The lesion is described as flat · no constitutional symptoms were reported · the patient notes bothersome appearance · the affected area is the top or side of the foot · female patient, age 40–49 · this is a close-up image · self-categorized by the patient as a rash · present for three to twelve months — 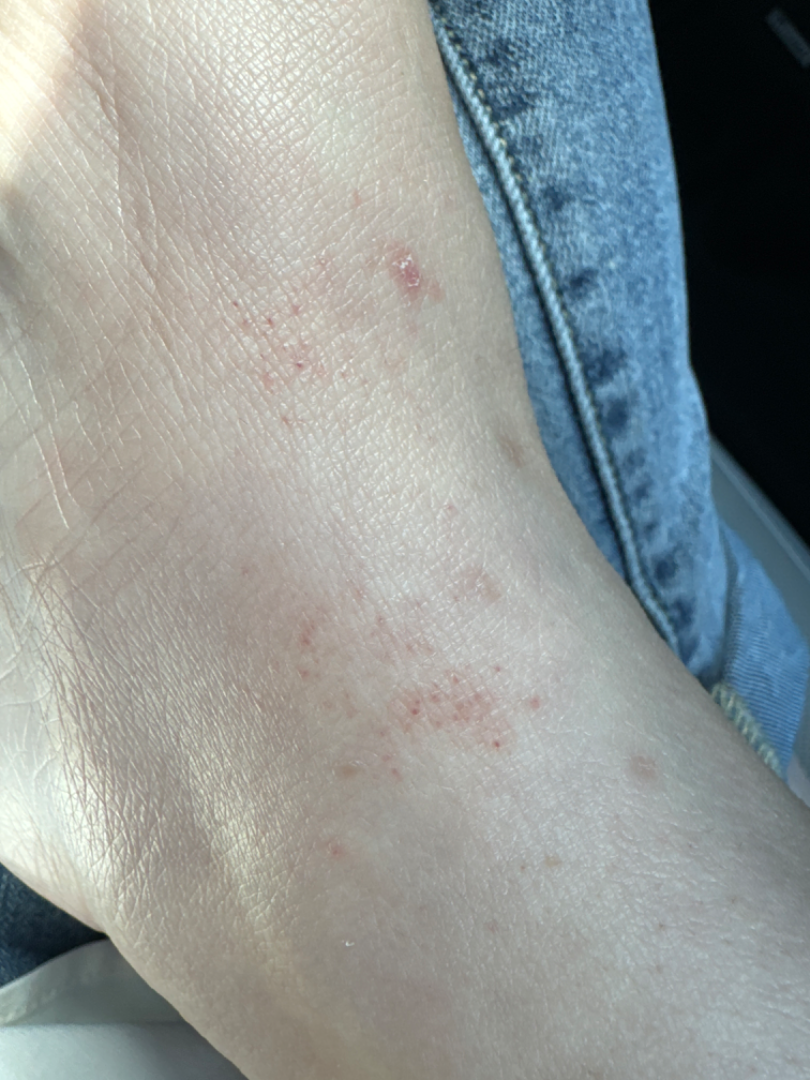Case summary:
– clinical impression · the differential includes Pigmented purpuric eruption and Eczema, with no clear leading consideration